A skin lesion imaged with a dermatoscope — 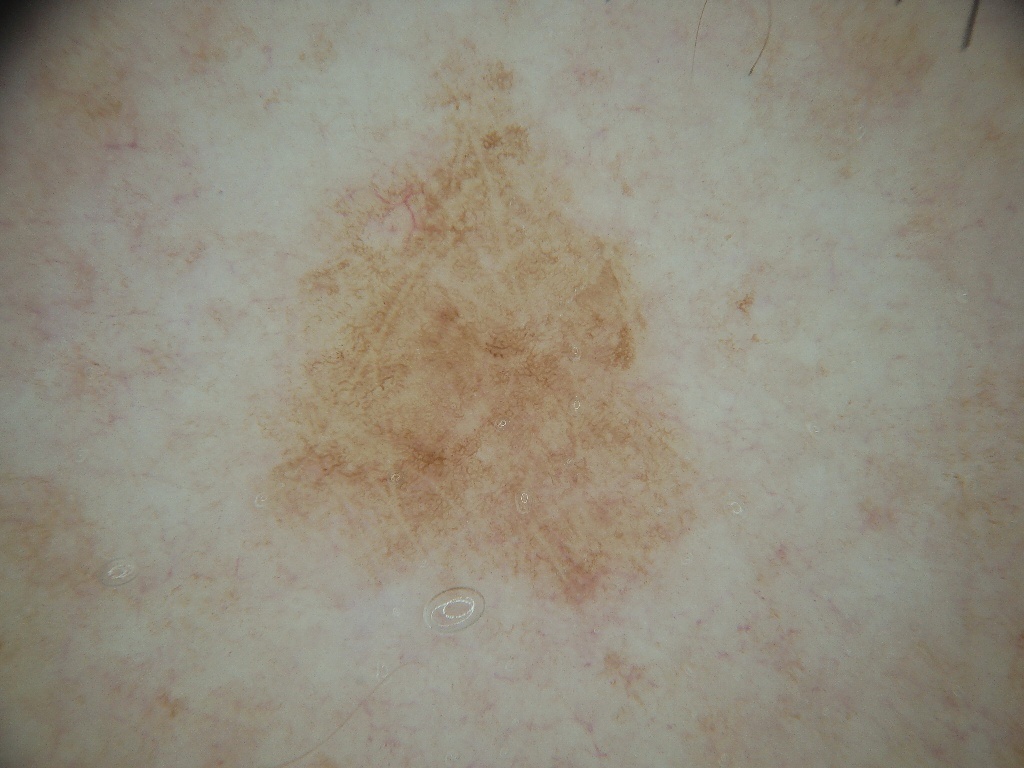Summary:
Dermoscopically, the lesion shows no streaks or globules. The lesion spans [264, 51, 693, 609].
Impression:
Clinically diagnosed as a benign skin lesion.